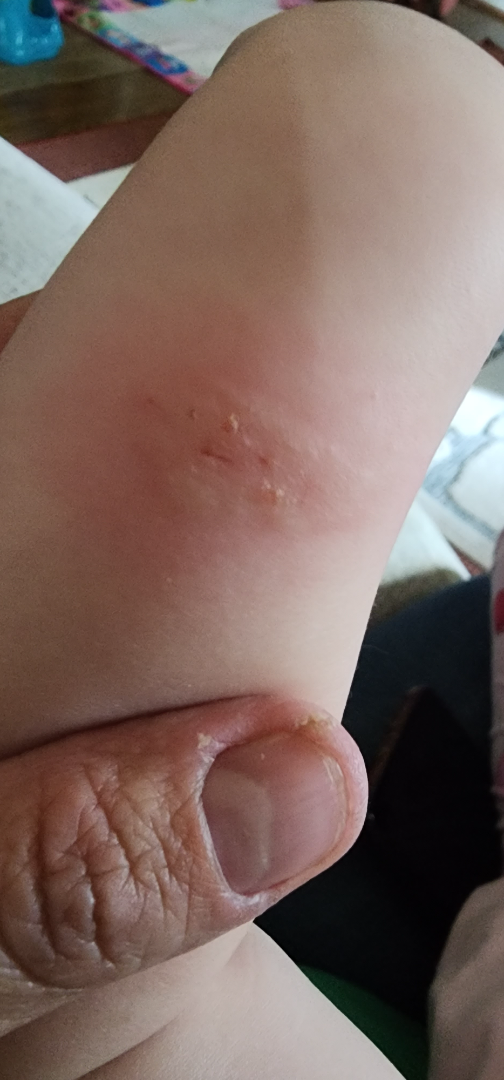The reviewer was unable to grade this case for skin condition. This is a close-up image.